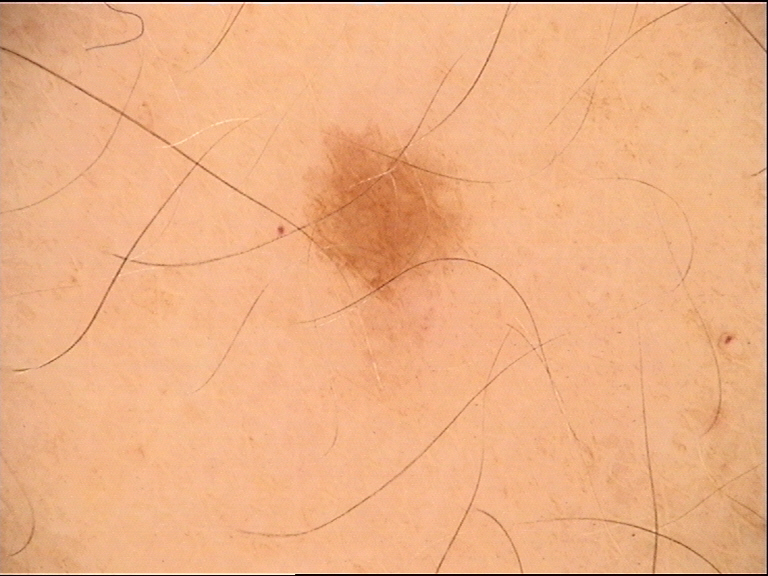A dermoscopic photograph of a skin lesion.
The architecture is that of a banal lesion.
Classified as a junctional nevus.